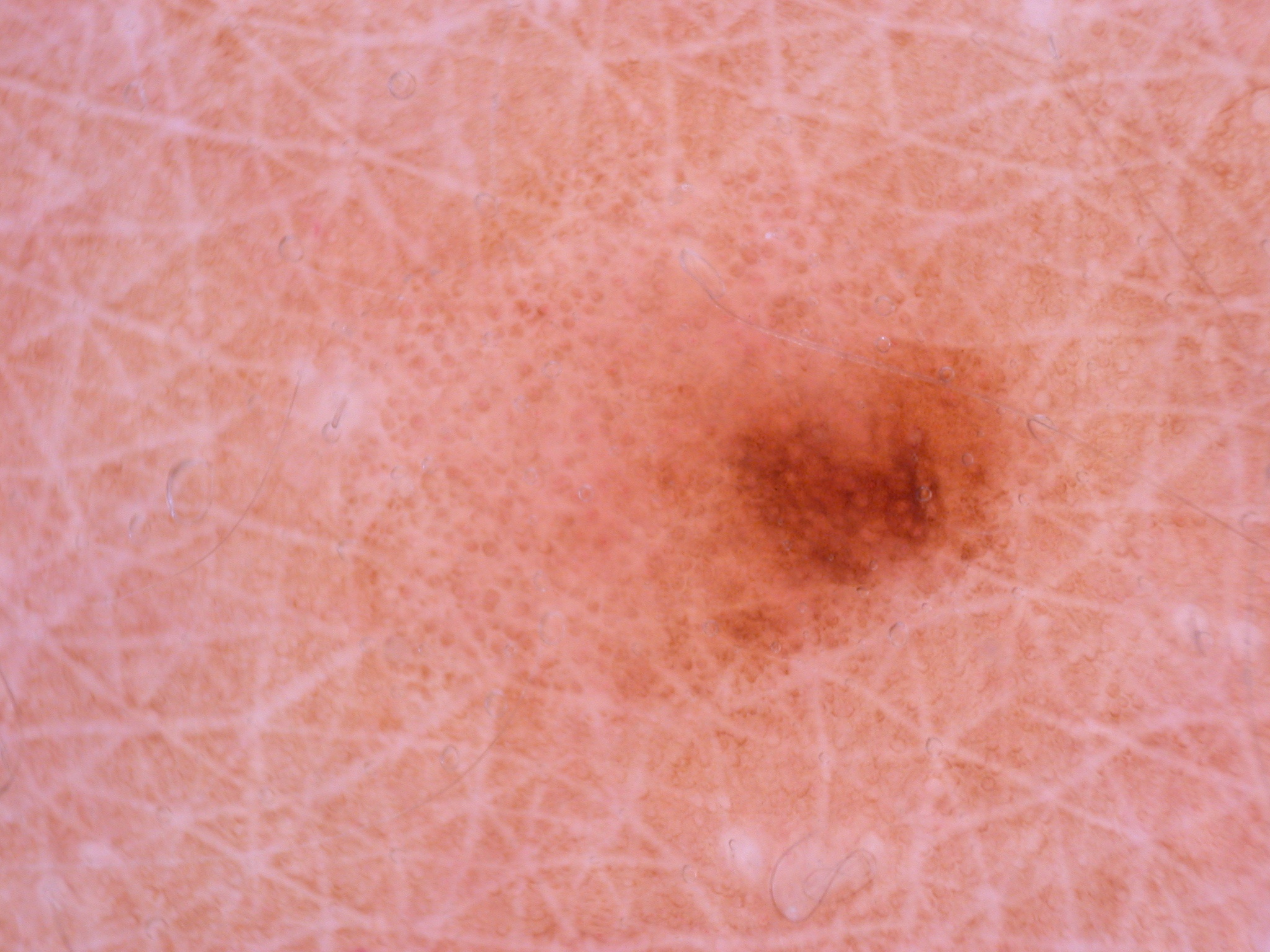<record>
<image>
  <modality>dermoscopy</modality>
</image>
<dermoscopic_features>
  <present>pigment network</present>
  <absent>milia-like cysts, globules, streaks, negative network</absent>
</dermoscopic_features>
<lesion_location>
  <bbox_xyxy>300, 131, 1057, 732</bbox_xyxy>
</lesion_location>
<diagnosis>
  <name>melanocytic nevus</name>
  <malignancy>benign</malignancy>
  <lineage>melanocytic</lineage>
  <provenance>clinical</provenance>
</diagnosis>
</record>